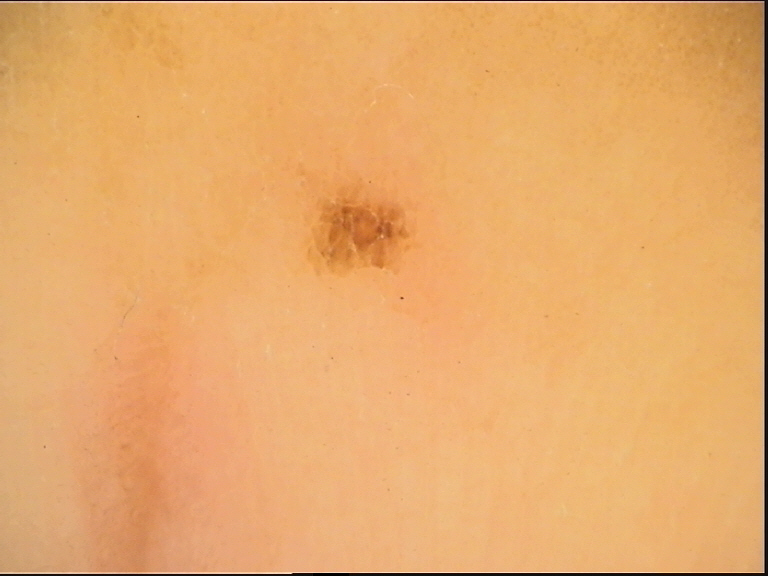Summary:
A dermoscopic image of a skin lesion.
Impression:
Consistent with an acral dysplastic junctional nevus.